A skin lesion imaged with a dermatoscope.
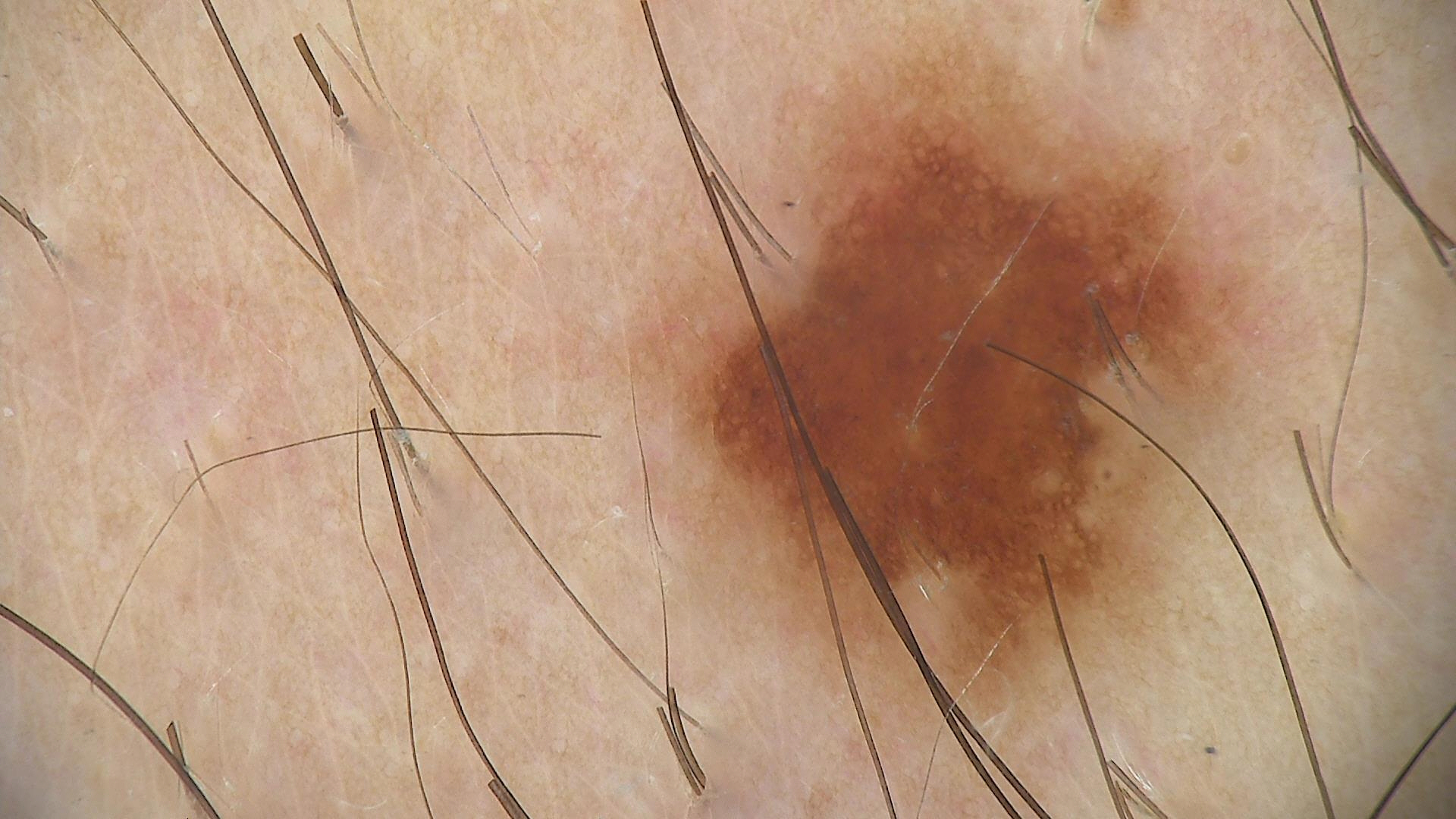<lesion>
<diagnosis>
<name>dysplastic junctional nevus</name>
<code>jd</code>
<malignancy>benign</malignancy>
<super_class>melanocytic</super_class>
<confirmation>expert consensus</confirmation>
</diagnosis>
</lesion>